A dermoscopy image of a single skin lesion.
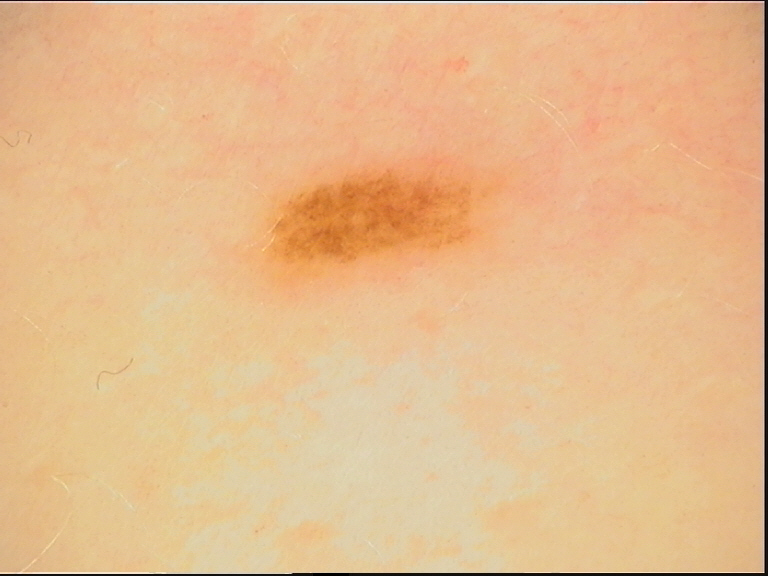<case>
<lesion_type>
<main_class>banal</main_class>
<pattern>junctional</pattern>
</lesion_type>
<diagnosis>
<name>junctional nevus</name>
<code>jb</code>
<malignancy>benign</malignancy>
<super_class>melanocytic</super_class>
<confirmation>expert consensus</confirmation>
</diagnosis>
</case>